Located on the head or neck, arm and leg · the subject is a female aged 40–49 · this is a close-up image: 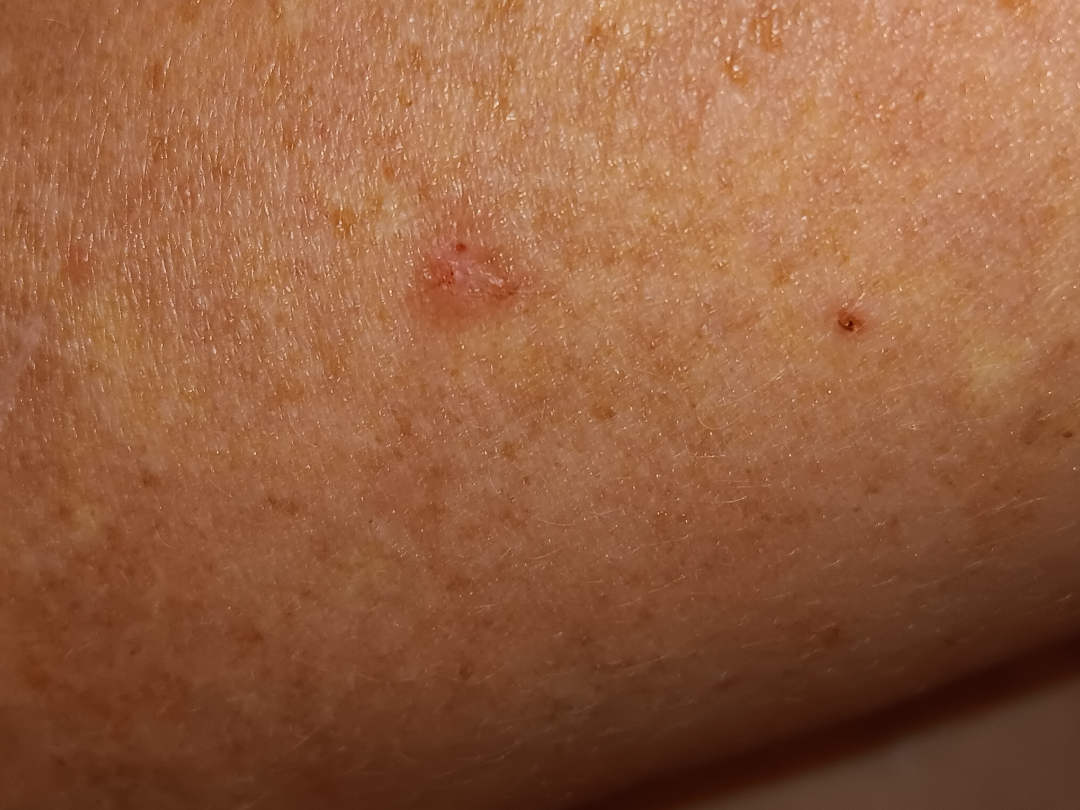diagnostic considerations: most consistent with Actinic Keratosis; possibly Herpes Zoster; also raised was Eczema; lower on the differential is Inflicted skin lesions; less likely is SCC/SCCIS.